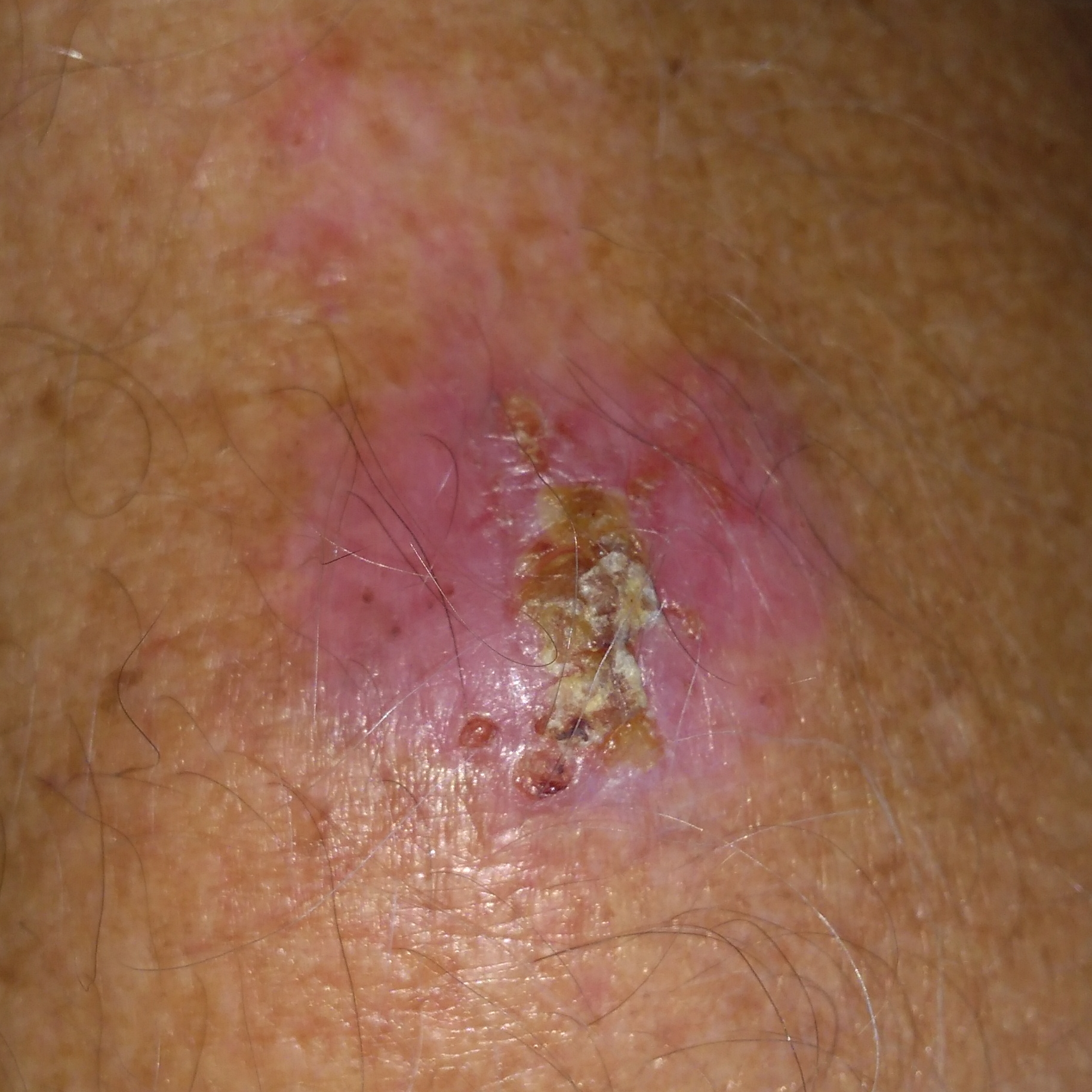| feature | finding |
|---|---|
| risk factors | prior malignancy (patient or family), pesticide exposure, alcohol use |
| image type | smartphone clinical photo |
| Fitzpatrick | II |
| subject | male, in their early 60s |
| location | the chest |
| lesion diameter | 40 × 20 mm |
| symptoms | growth, pain, elevation, bleeding, itching |
| pathology | basal cell carcinoma (biopsy-proven) |